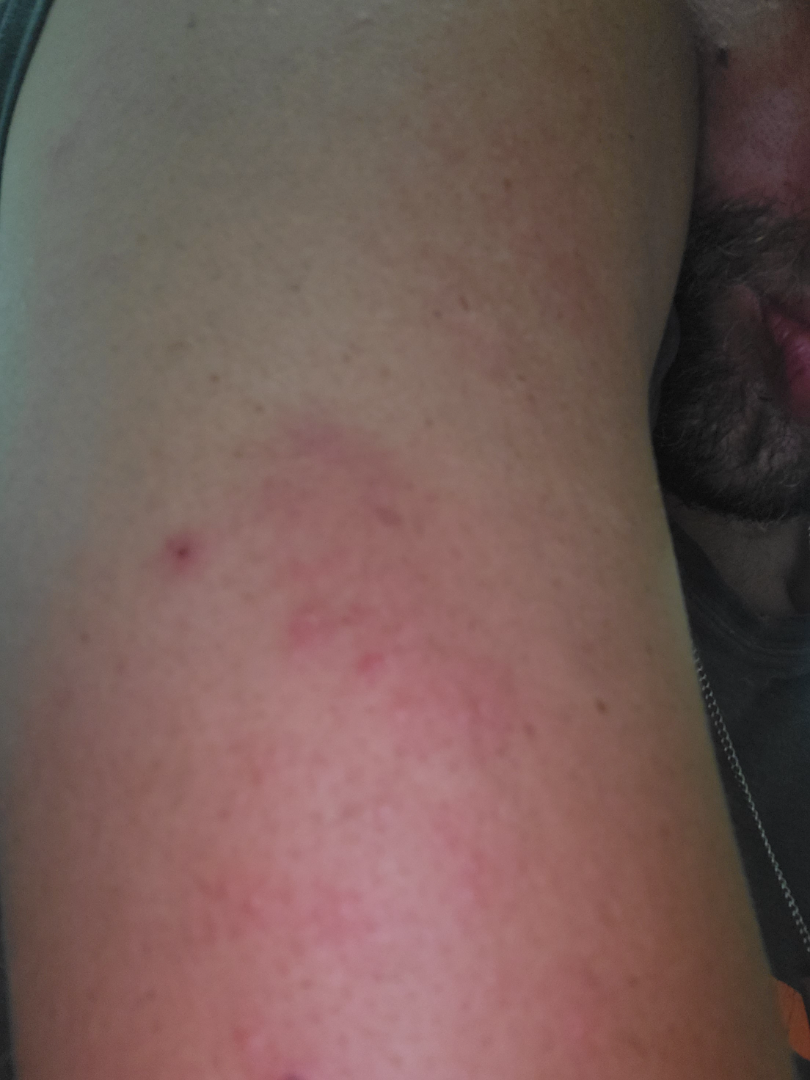assessment: ungradable on photographic review.